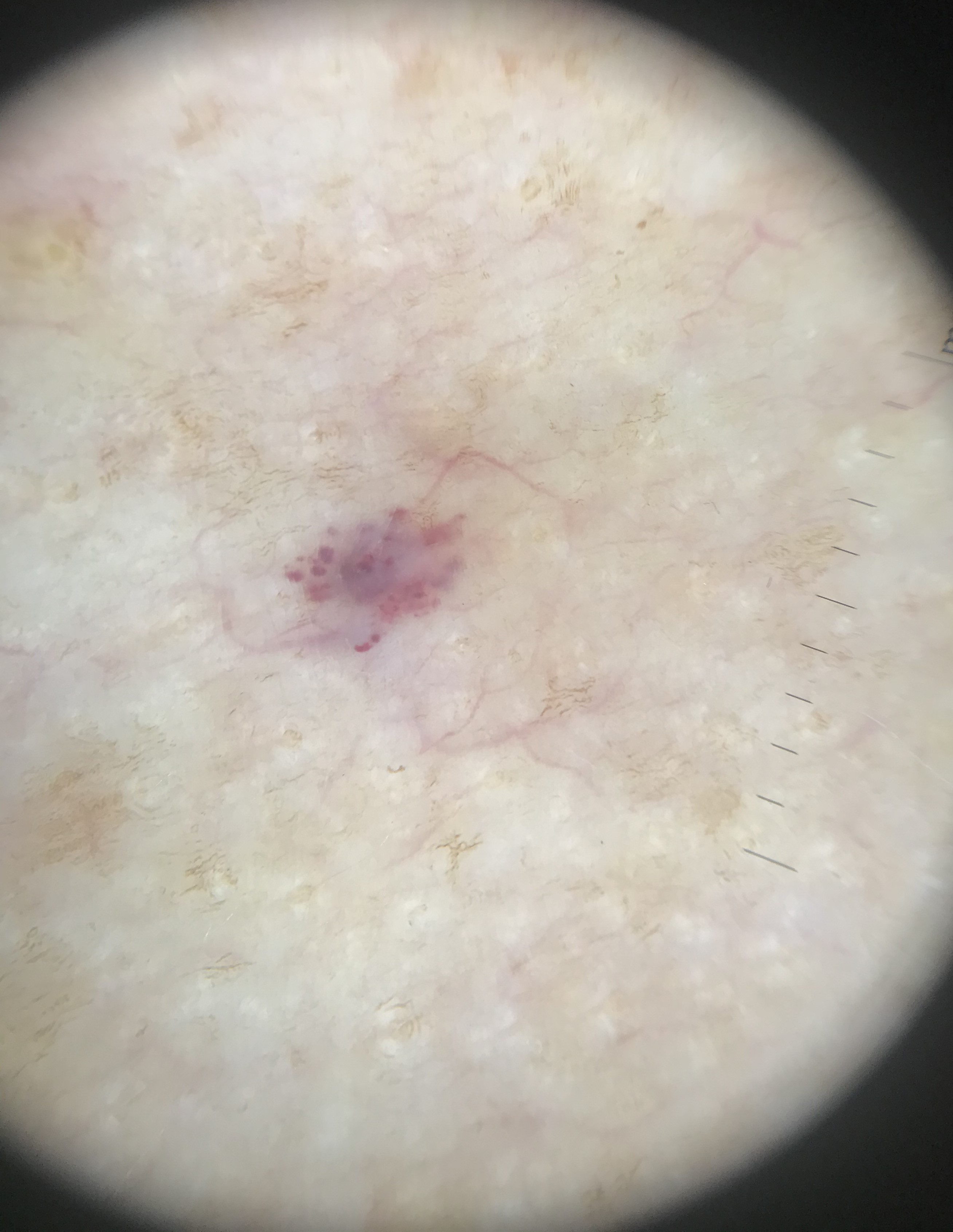| field | value |
|---|---|
| assessment | lymphangioma (expert consensus) |